A male patient, aged 8 to 12. A dermoscopy image of a single skin lesion: 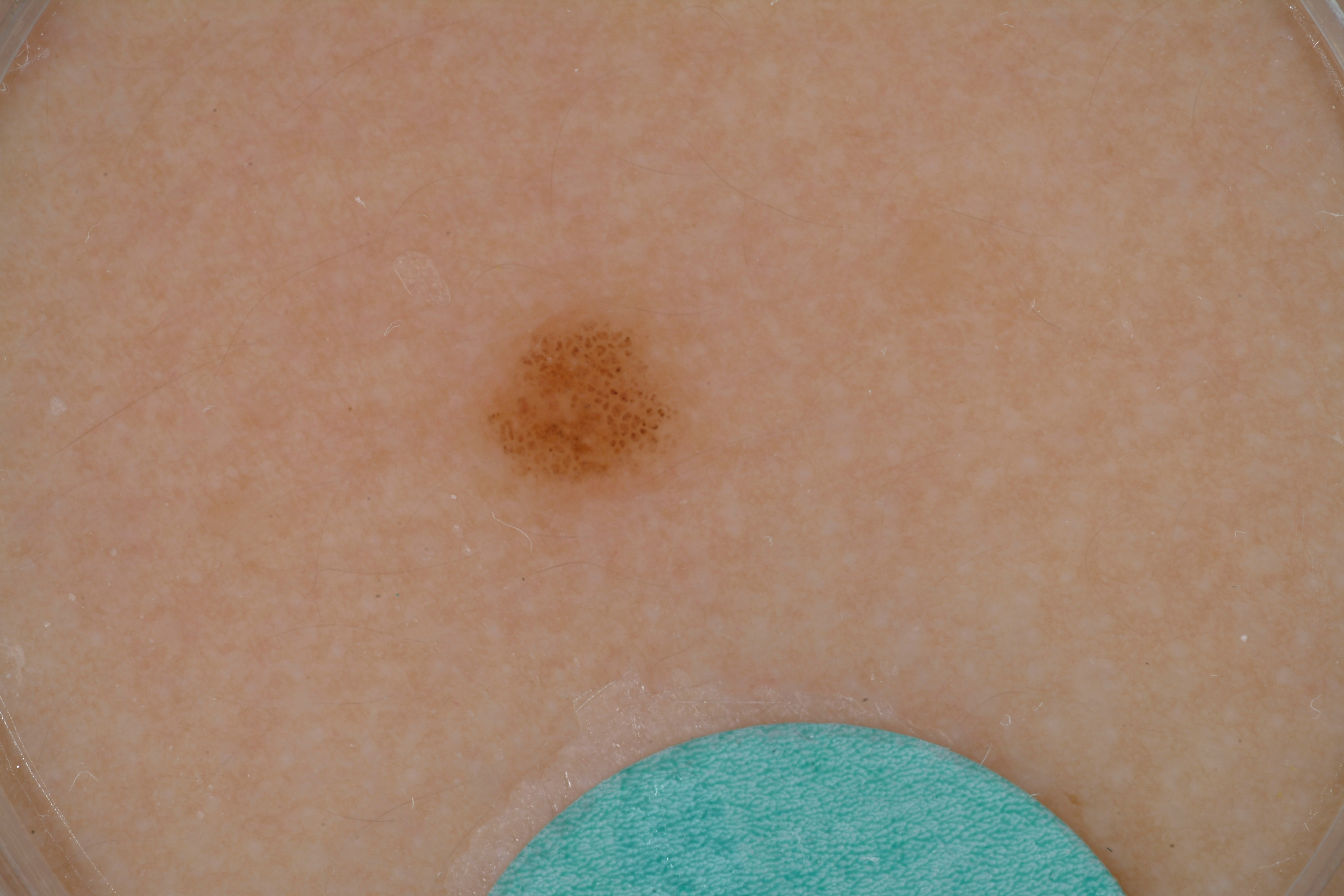As (left, top, right, bottom), the visible lesion spans [469,307,710,510]. Dermoscopic assessment notes no milia-like cysts, negative network, pigment network, or streaks. A small lesion within a wider field of skin. The lesion was assessed as a melanocytic nevus, a benign skin lesion.